Dermoscopy of a skin lesion:
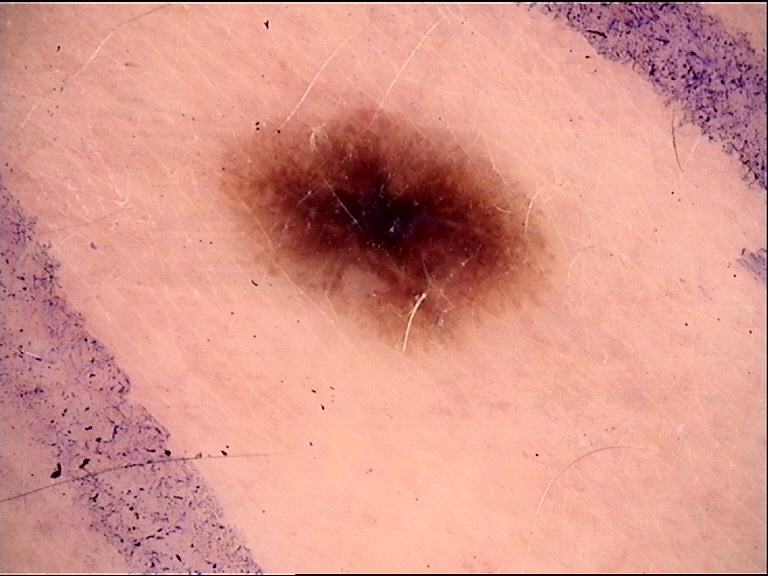The diagnostic label was a dysplastic junctional nevus.